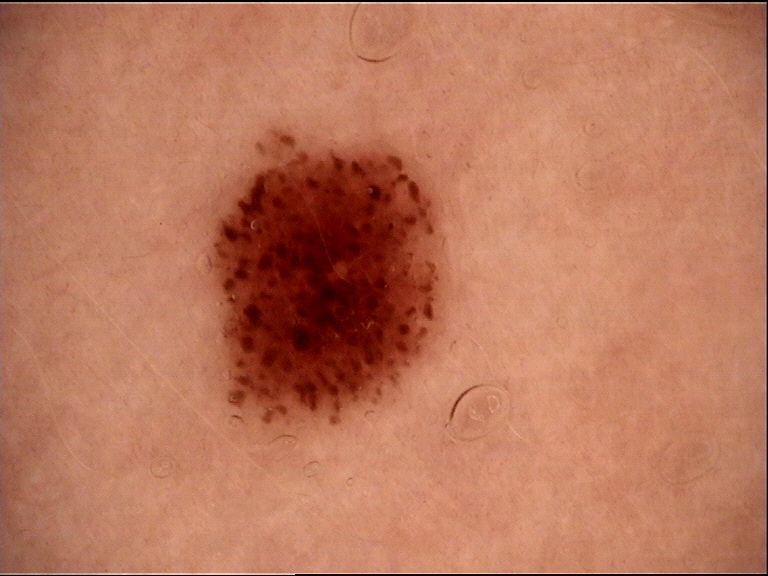Diagnosed as a compound nevus.